Dermoscopy of a skin lesion: 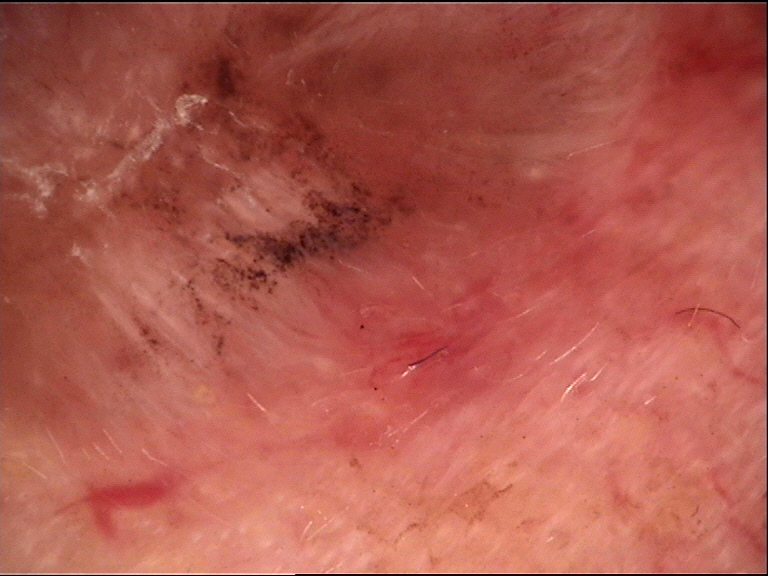{
  "lesion_type": {
    "main_class": "keratinocytic"
  },
  "diagnosis": {
    "name": "basal cell carcinoma",
    "code": "bcc",
    "malignancy": "malignant",
    "super_class": "non-melanocytic",
    "confirmation": "histopathology"
  }
}